The lesion involves the leg, front of the torso, back of the torso and arm. The photograph is a close-up of the affected area: 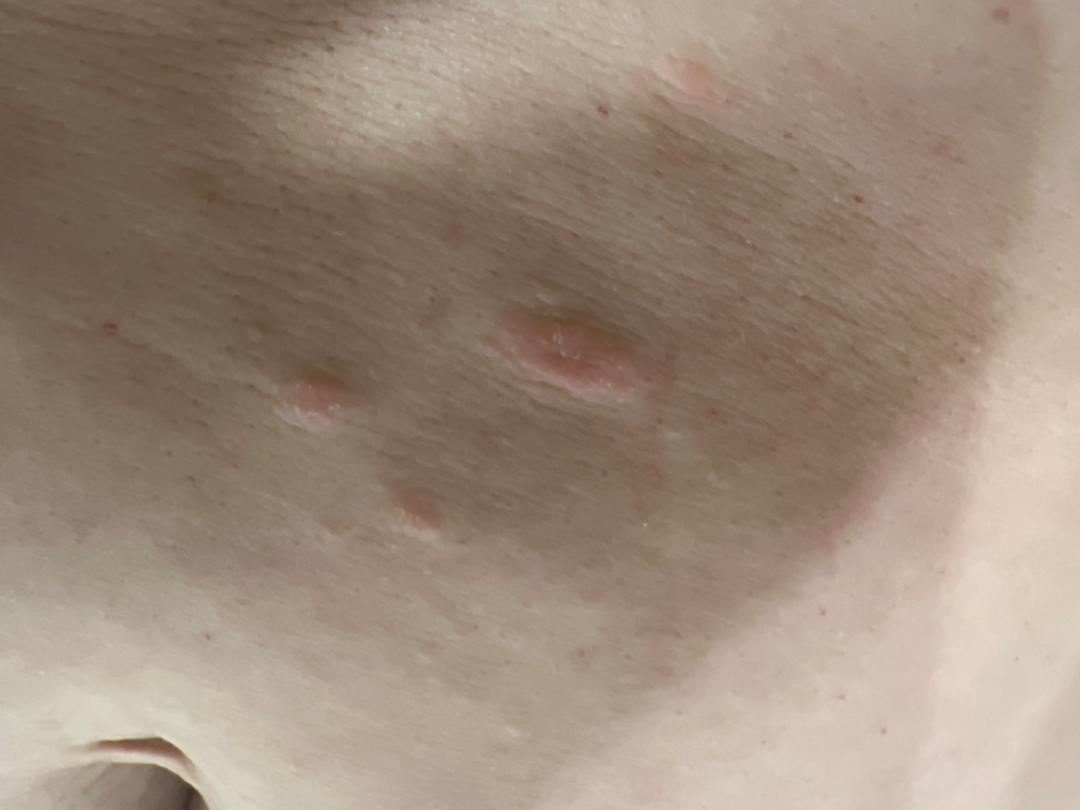Findings:
• assessment — ungradable on photographic review
• self-categorized as — a rash
• other reported symptoms — none reported
• described texture — raised or bumpy and rough or flaky
• present for — one to four weeks